Dermoscopy of a skin lesion: 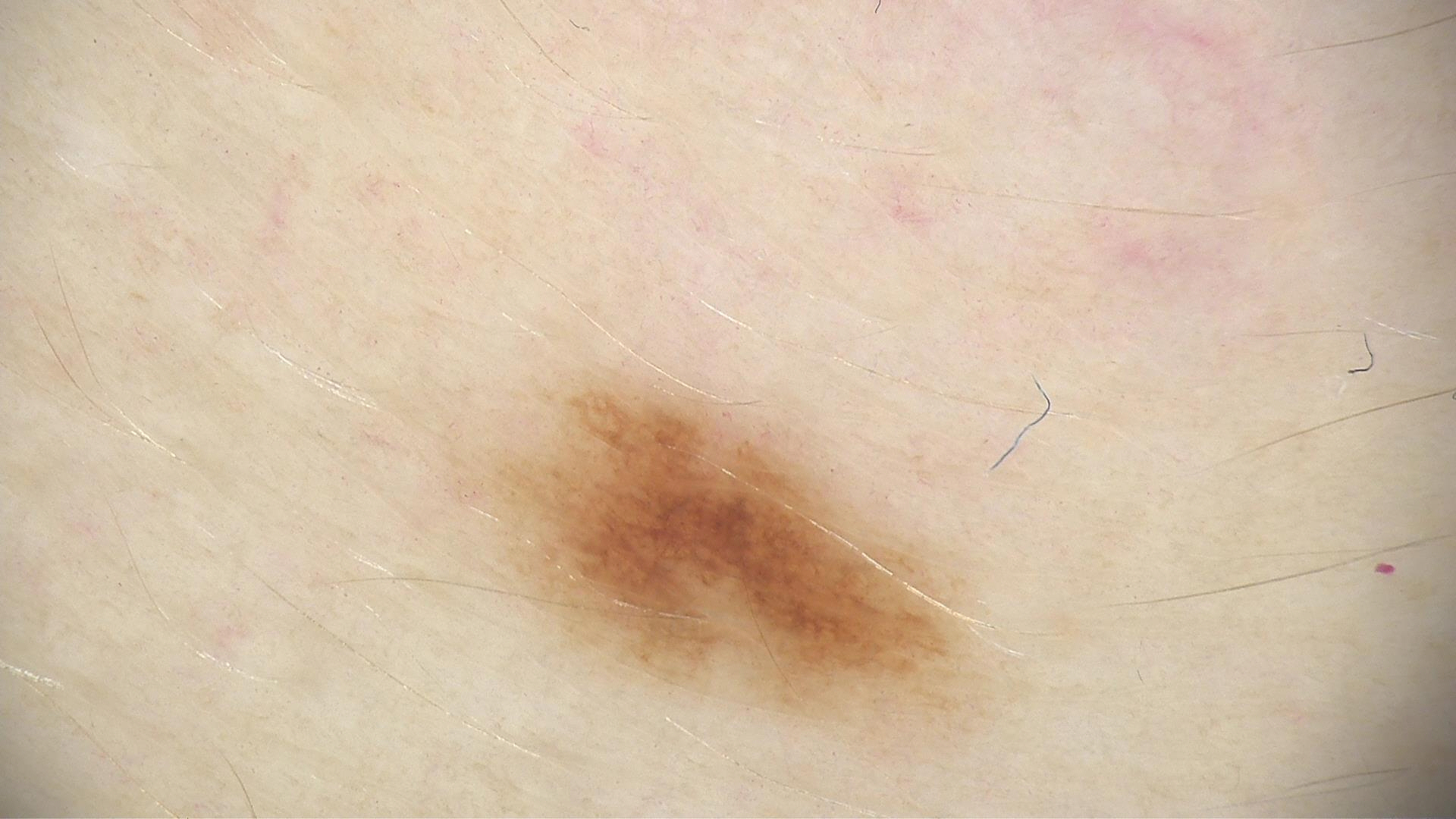<lesion>
  <diagnosis>
    <name>dysplastic junctional nevus</name>
    <code>jd</code>
    <malignancy>benign</malignancy>
    <super_class>melanocytic</super_class>
    <confirmation>expert consensus</confirmation>
  </diagnosis>
</lesion>